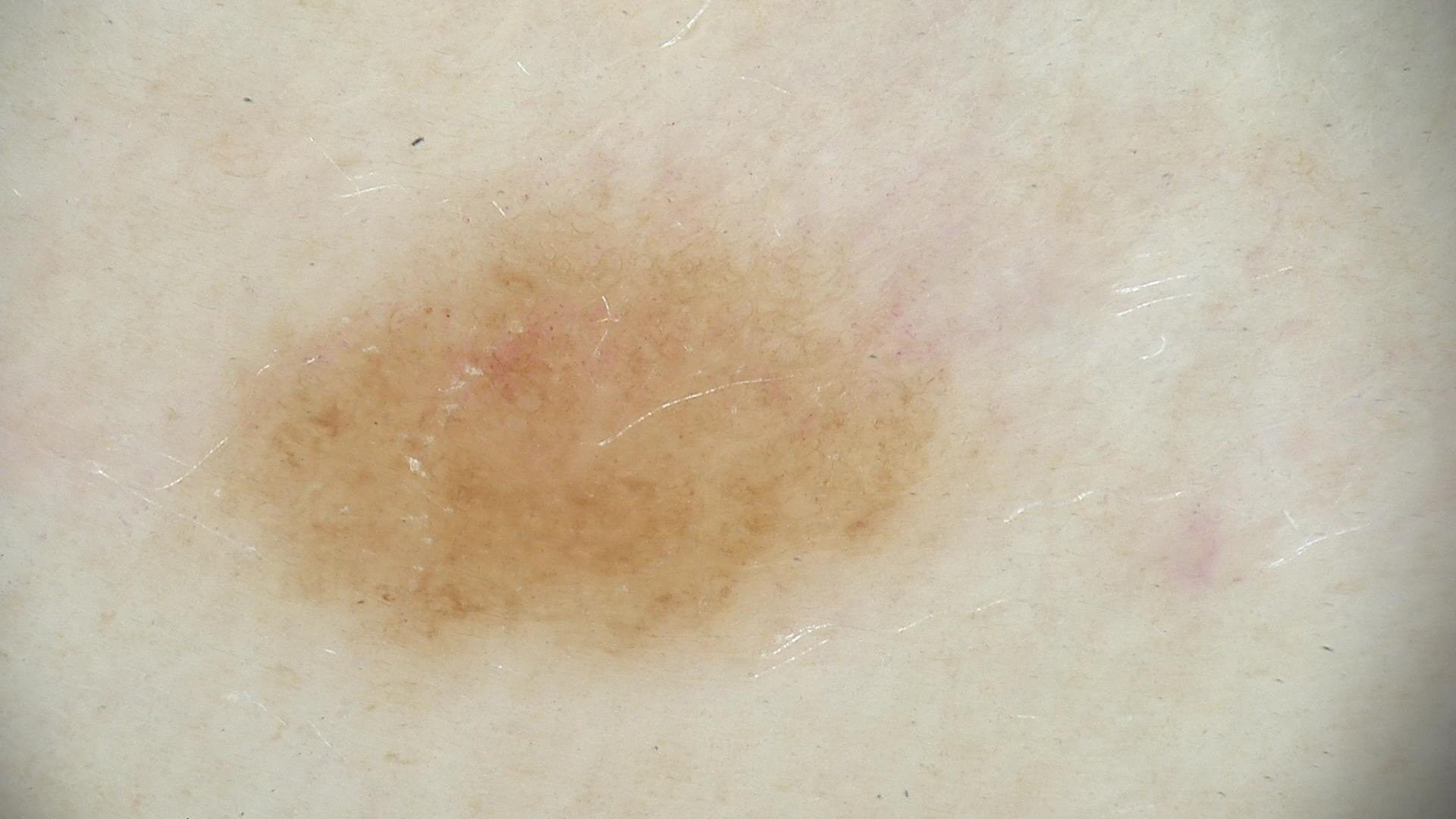| key | value |
|---|---|
| assessment | dysplastic junctional nevus (expert consensus) |